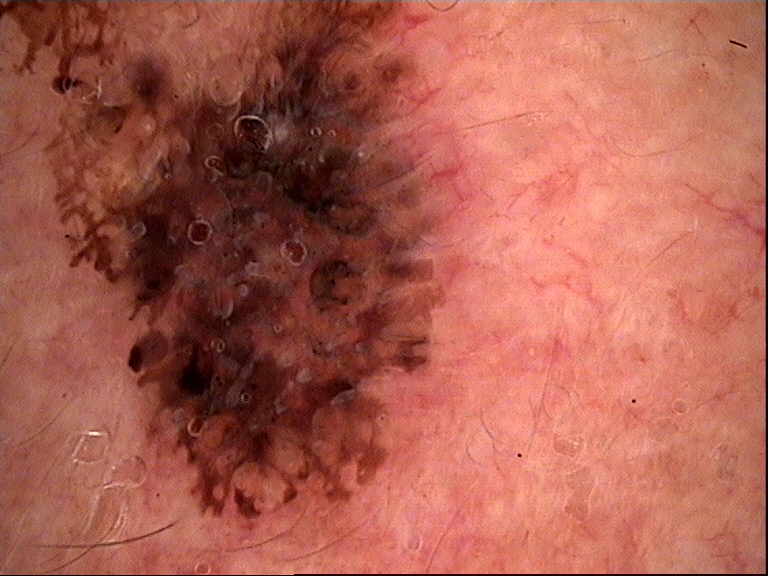Summary:
Dermoscopy of a skin lesion. The architecture is that of a keratinocytic lesion.
Conclusion:
Labeled as a benign lesion — a seborrheic keratosis.